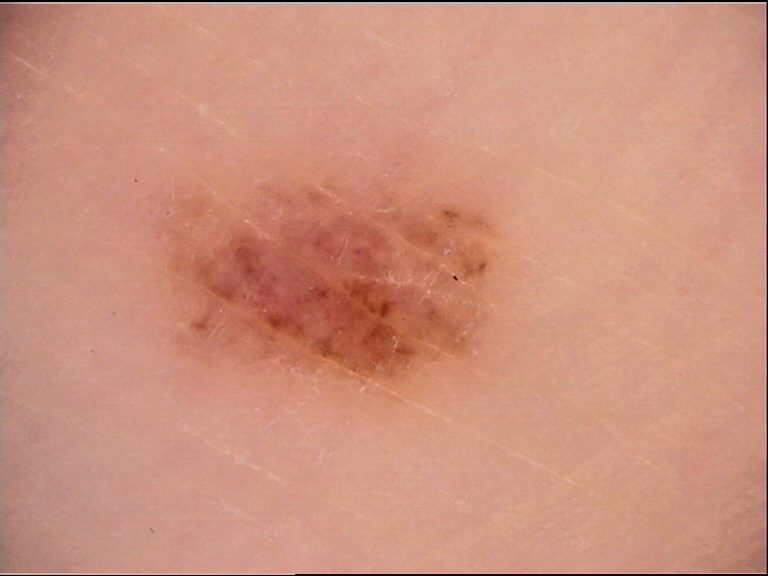{
  "image": "dermatoscopy",
  "diagnosis": {
    "name": "junctional nevus",
    "code": "jb",
    "malignancy": "benign",
    "super_class": "melanocytic",
    "confirmation": "expert consensus"
  }
}